A dermoscopic close-up of a skin lesion · a female patient aged 73-77 · the chart records no first-degree relative with melanoma and no prior melanoma: 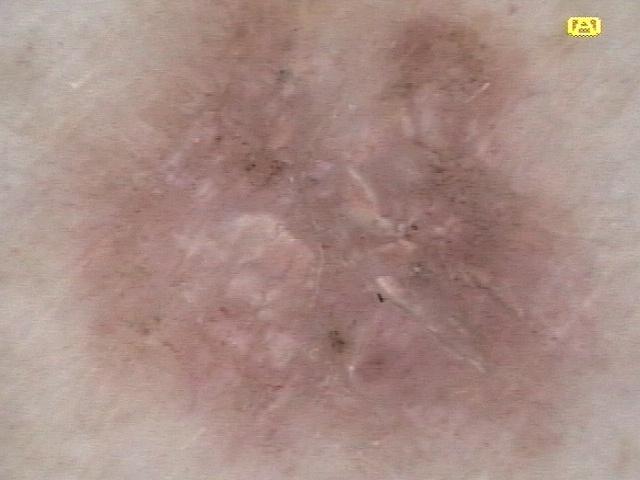Located on a lower extremity. The biopsy diagnosis was a tumor of follicular differentiation — a basal cell carcinoma.